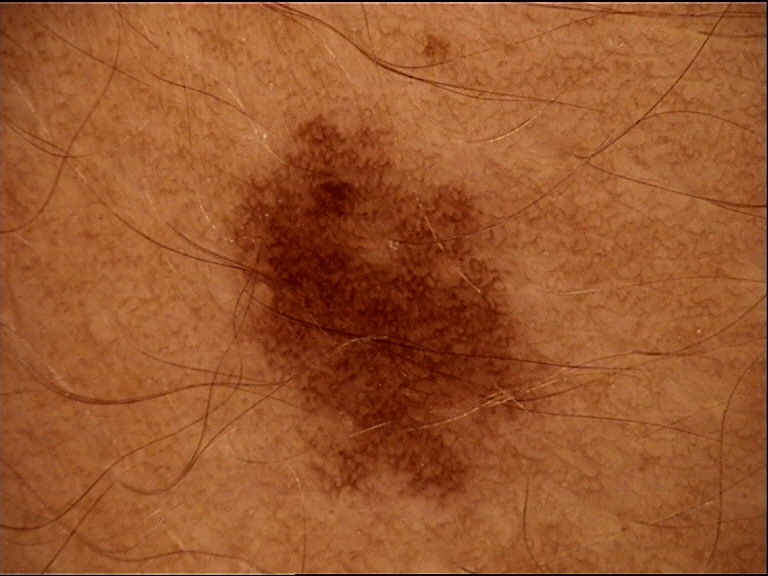| feature | finding |
|---|---|
| diagnosis | dysplastic junctional nevus (expert consensus) |